Located on the head or neck; a close-up photograph.
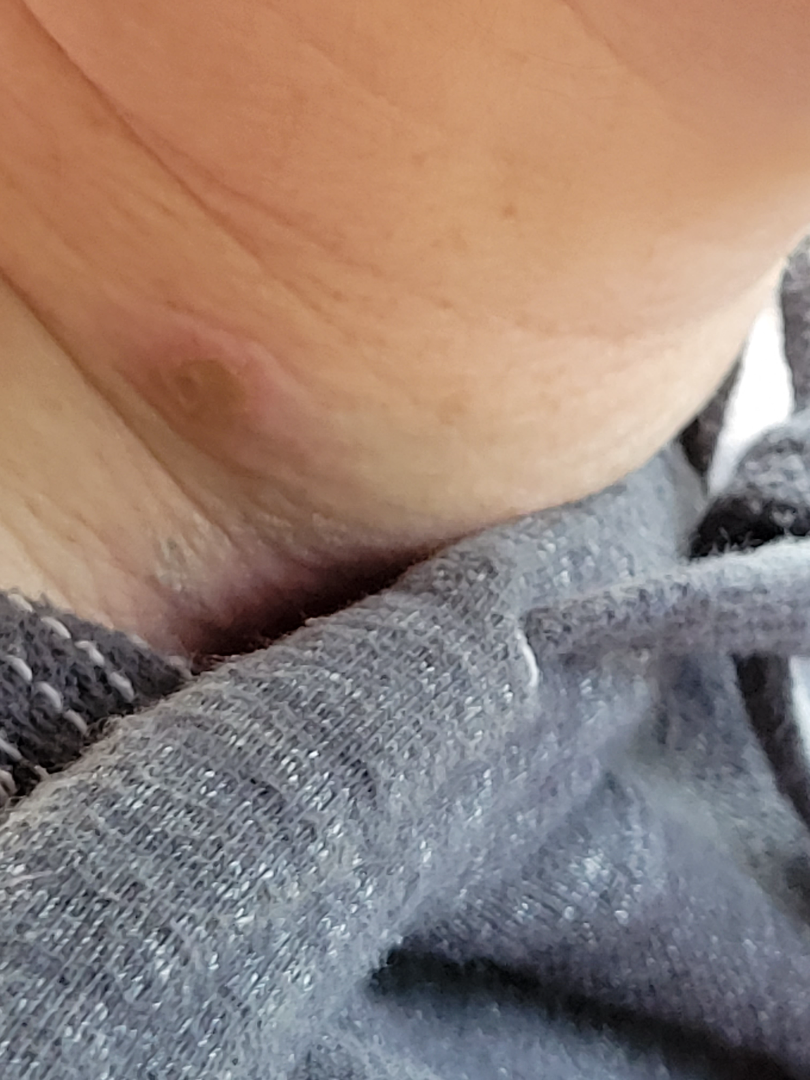<report>
  <assessment>indeterminate from the photograph</assessment>
  <texture>rough or flaky</texture>
  <duration>about one day</duration>
  <symptoms>bothersome appearance</symptoms>
  <systemic_symptoms>none reported</systemic_symptoms>
</report>